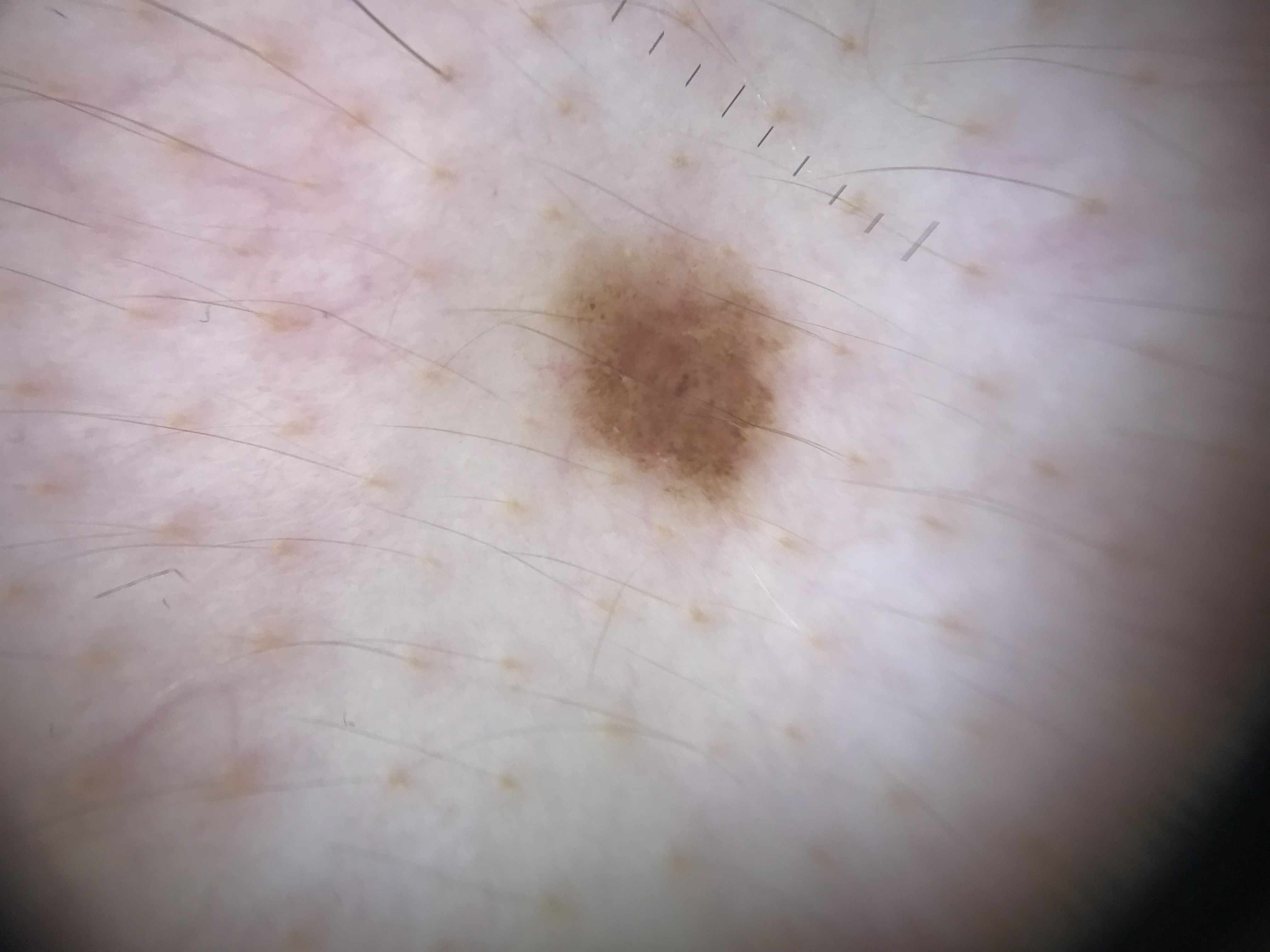Case: A skin lesion imaged with a dermatoscope. Conclusion: Classified as a dysplastic junctional nevus.